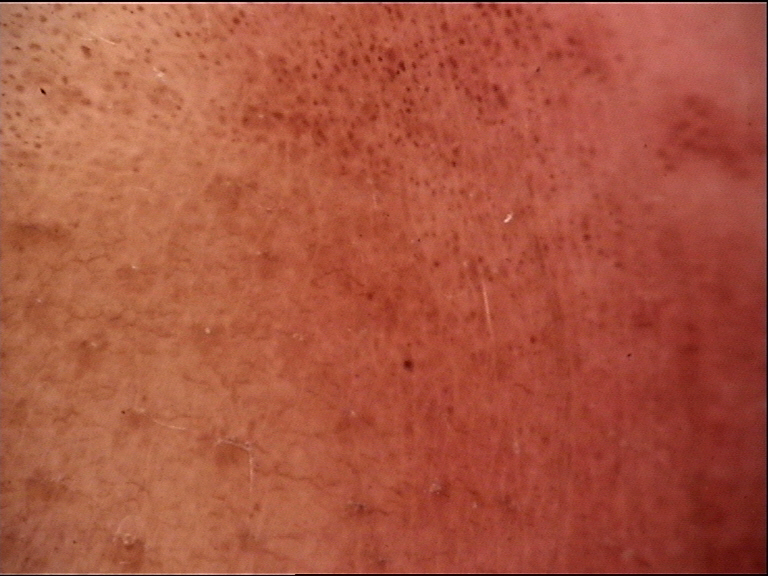modality: dermatoscopy, diagnostic label: congenital junctional nevus (expert consensus).